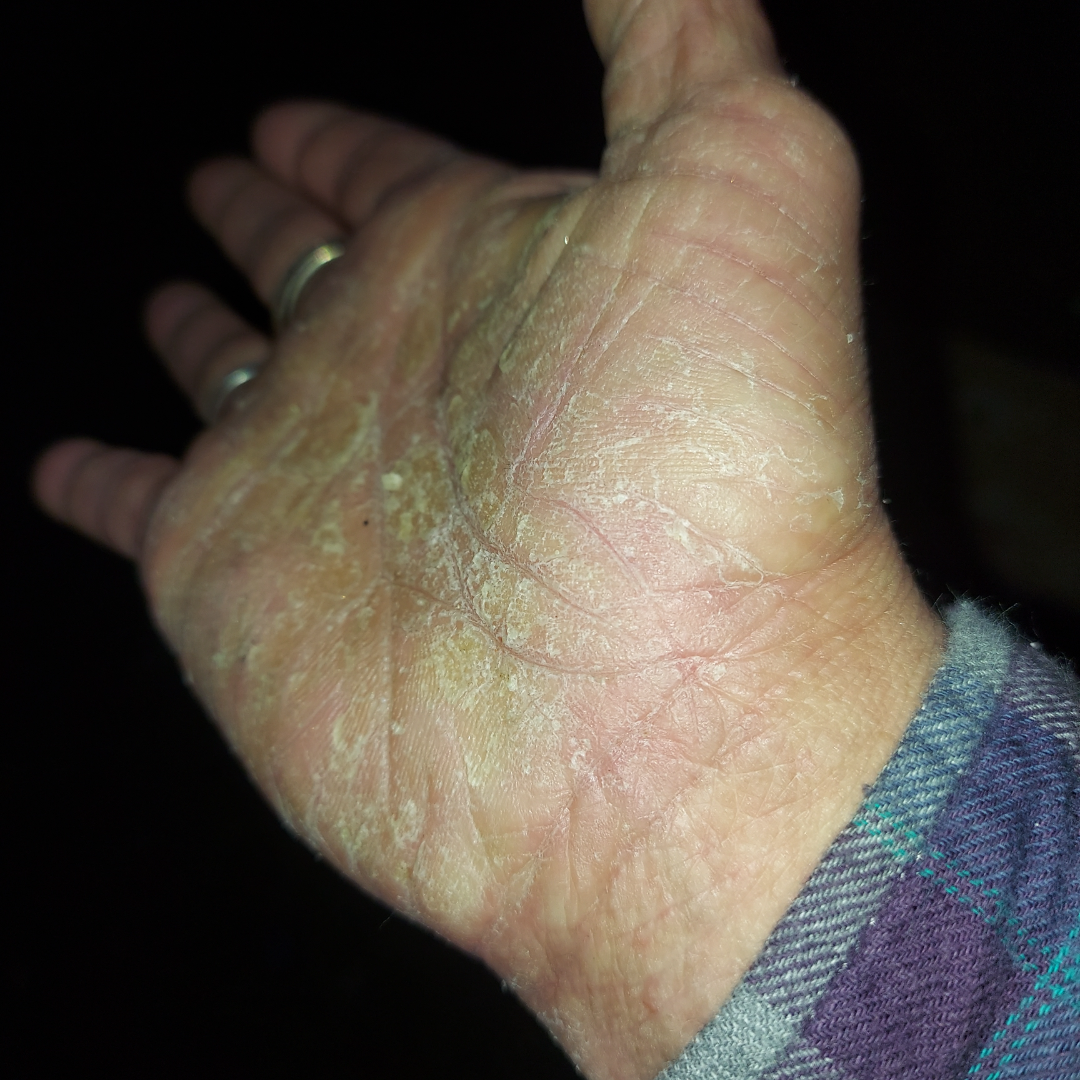The patient reports the condition has been present for more than one year.
The patient considered this a rash.
An image taken at an angle.
Located on the palm.
The patient is a female aged 40–49.
Texture is reported as rough or flaky.
The lesion is associated with itching, bothersome appearance, bleeding and pain.
On teledermatology review: most consistent with Eczema; an alternative is Hyperkeratosis; lower on the differential is Keratoderma.